A dermoscopic photograph of a skin lesion:
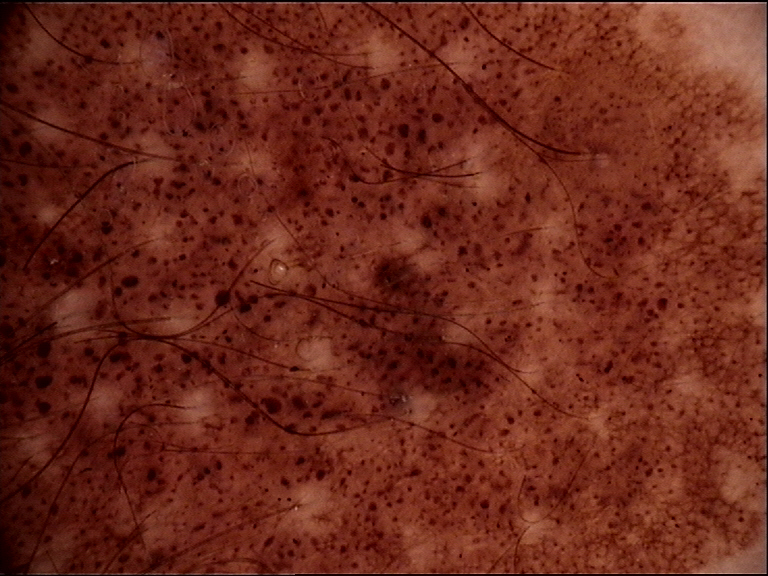subtype: banal | label: congenital compound nevus (expert consensus).